A close-up photograph · female contributor, age 30–39 · the back of the hand and head or neck are involved:
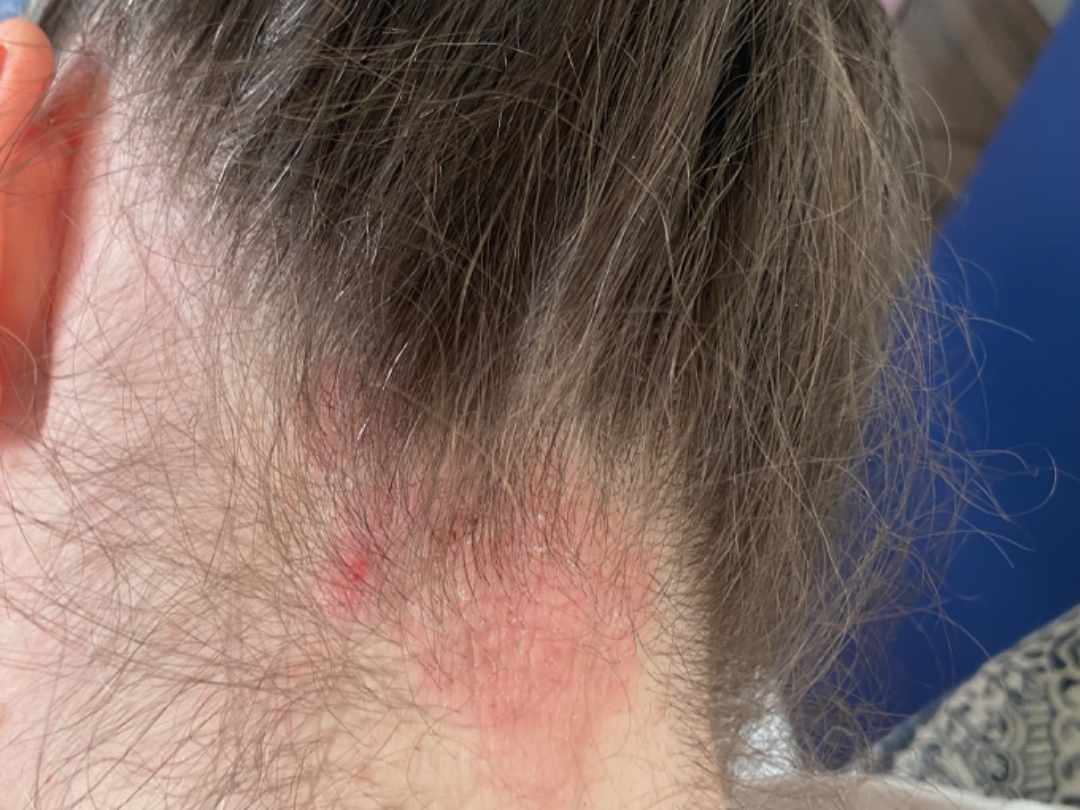On remote review of the image, most consistent with Eczema; an alternative is Psoriasis.